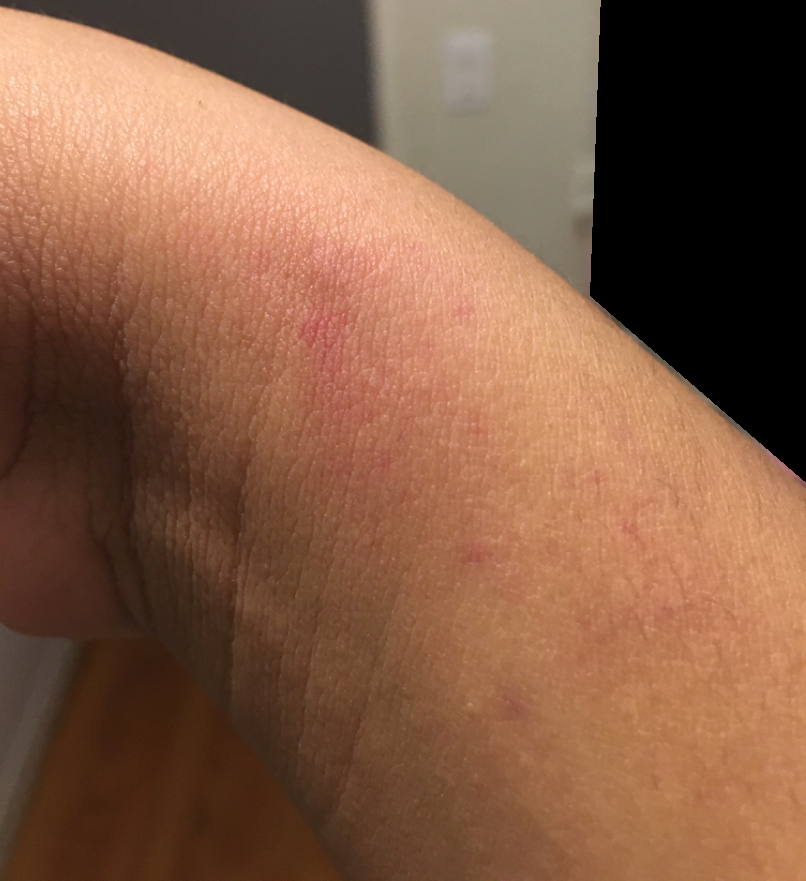framing = close-up, patient describes the issue as = a rash, systemic symptoms = none reported, anatomic site = arm, symptoms = bothersome appearance, texture = flat, subject = female, dermatologist impression = reviewed remotely by one dermatologist: the leading consideration is Irritant Contact Dermatitis; the differential also includes Purpura.